The photograph was taken at an angle · male subject, age 30–39 · the lesion involves the arm, leg and front of the torso: 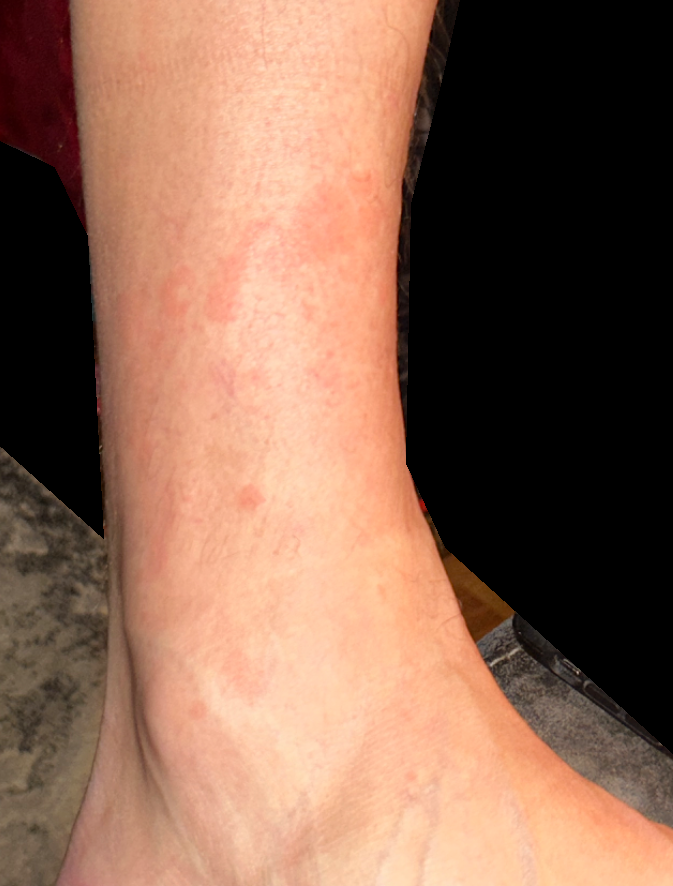A single dermatologist reviewed the case: Pityriasis rosea, Psoriasis and Eczema were each considered, in no particular order.